A patient in their 40s; a clinical photograph showing a skin lesion — 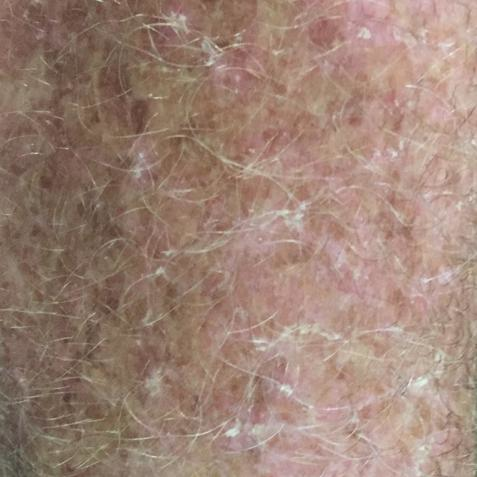Case summary: The lesion involves an arm. The patient reports that the lesion itches. Conclusion: Clinically diagnosed as an actinic keratosis.